A dermoscopy image of a single skin lesion; a male subject, aged 68-72: 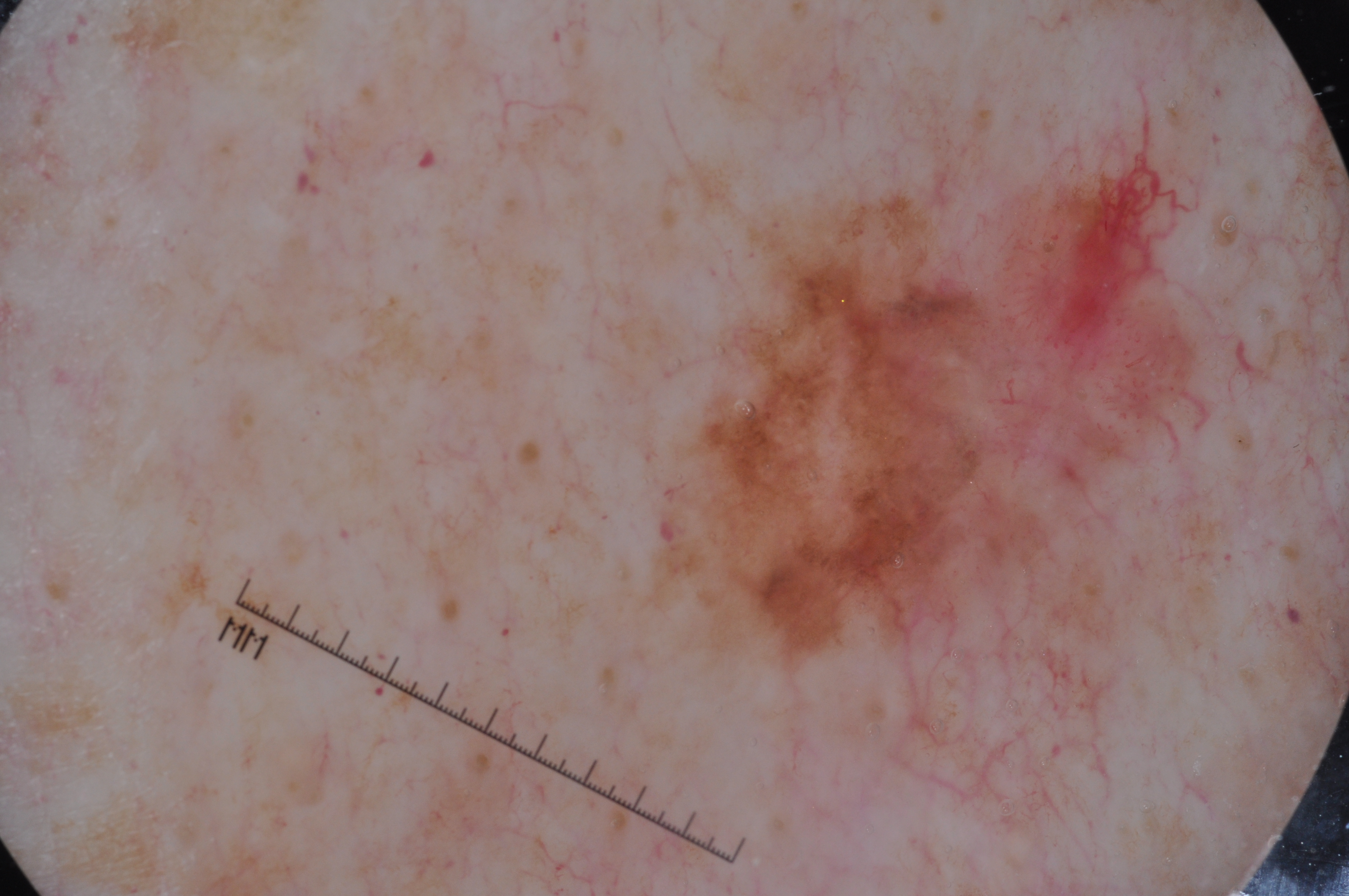<case>
<dermoscopic_features>
  <present>pigment network, milia-like cysts</present>
  <absent>streaks, negative network</absent>
</dermoscopic_features>
<lesion_extent>
  <approx_field_fraction_pct>25</approx_field_fraction_pct>
</lesion_extent>
<lesion_location>
  <bbox_xyxy>633, 69, 1263, 730</bbox_xyxy>
</lesion_location>
<diagnosis>
  <name>melanoma</name>
  <malignancy>malignant</malignancy>
  <lineage>melanocytic</lineage>
  <provenance>histopathology</provenance>
</diagnosis>
</case>